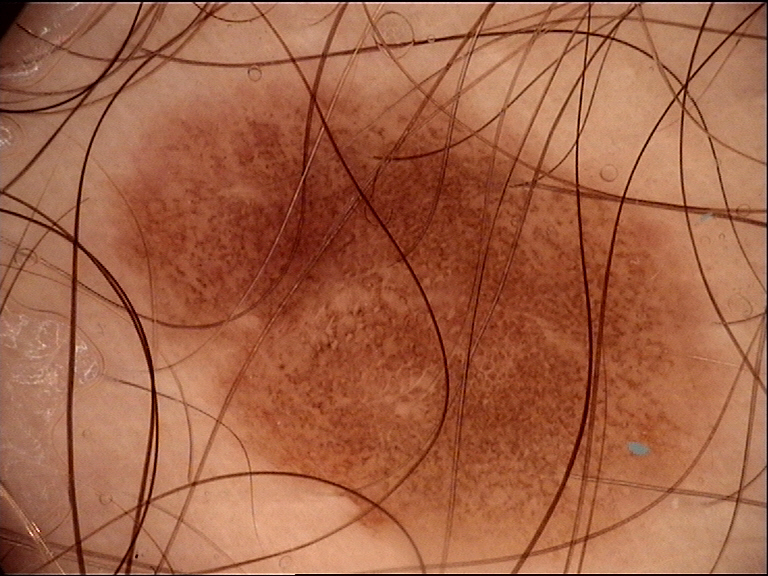Q: What is the imaging modality?
A: dermoscopy
Q: What is the diagnosis?
A: junctional nevus (expert consensus)